Located on the leg, texture is reported as flat, close-up view, no relevant lesion symptoms reported, the patient indicates the condition has been present for less than one week, no constitutional symptoms were reported, self-categorized by the patient as a rash.
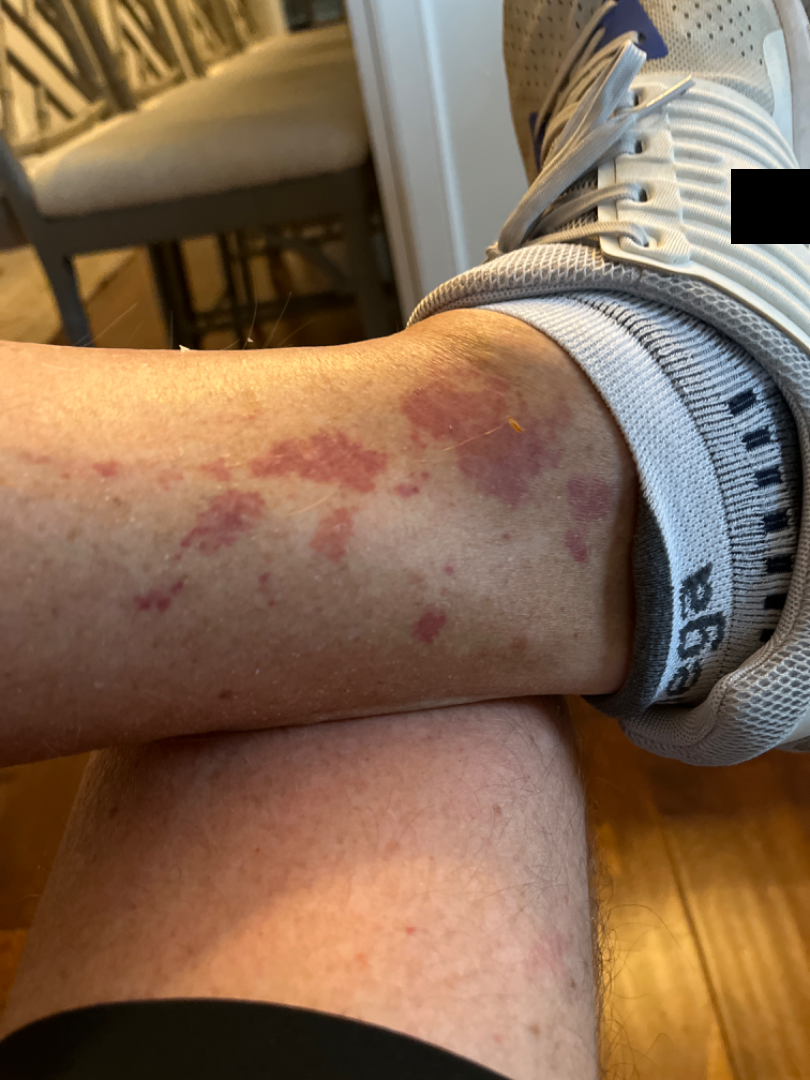No differential diagnosis could be assigned on photographic review.